The patient says their skin reddens with sun exposure · by self-report, a personal history of cancer, a personal history of skin cancer, and no prior organ transplant · few moles overall by the patient's own estimate · a female patient aged 71 · collected as part of a research study, without a referral diagnosis · a skin lesion imaged with a dermatoscope:
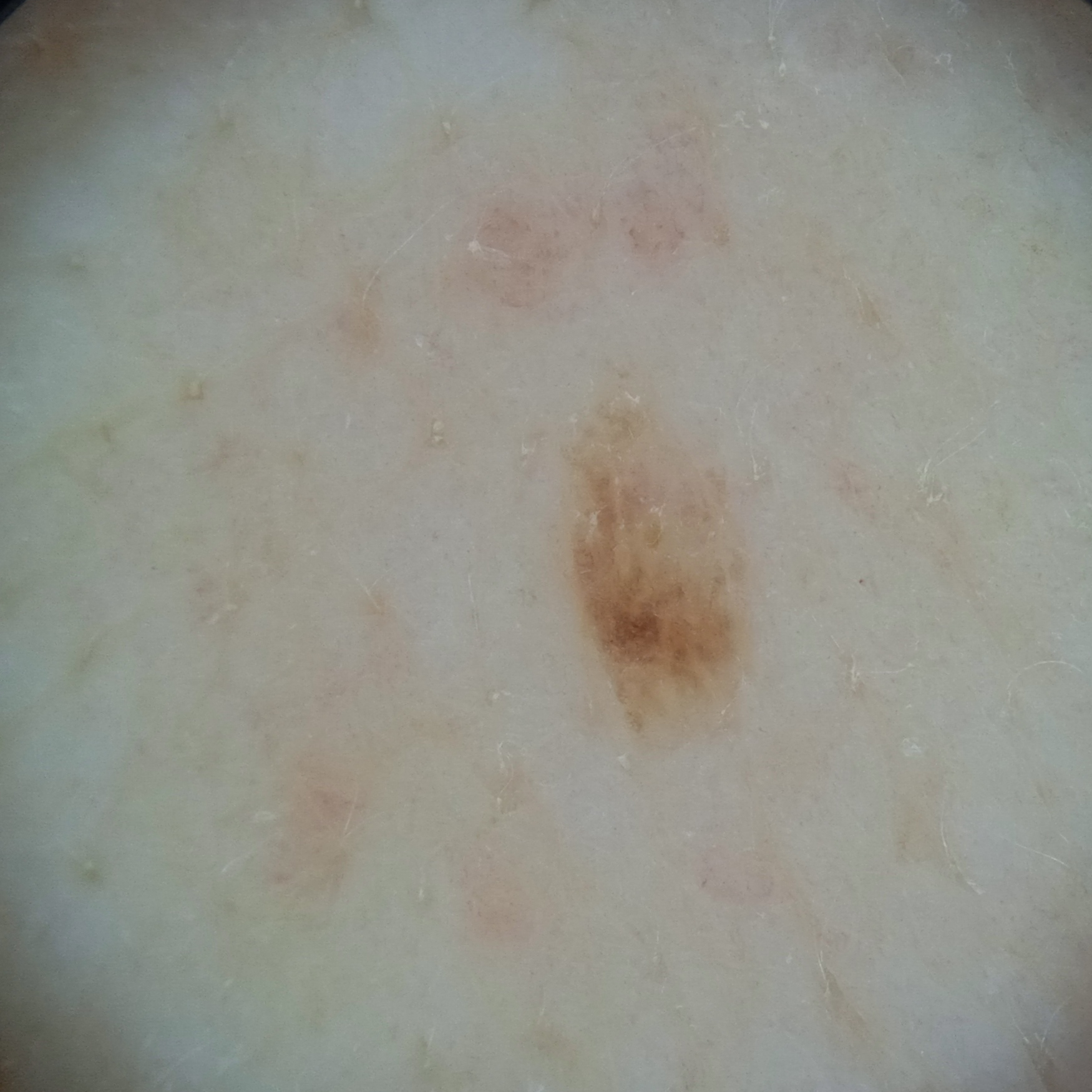{
  "lesion_location": "the back",
  "lesion_size": {
    "diameter_mm": 3.8
  },
  "diagnosis": {
    "name": "seborrheic keratosis",
    "malignancy": "benign",
    "unanimous": false,
    "certainty": "moderate"
  }
}